A dermoscopic close-up of a skin lesion; the subject is a female aged around 30 — 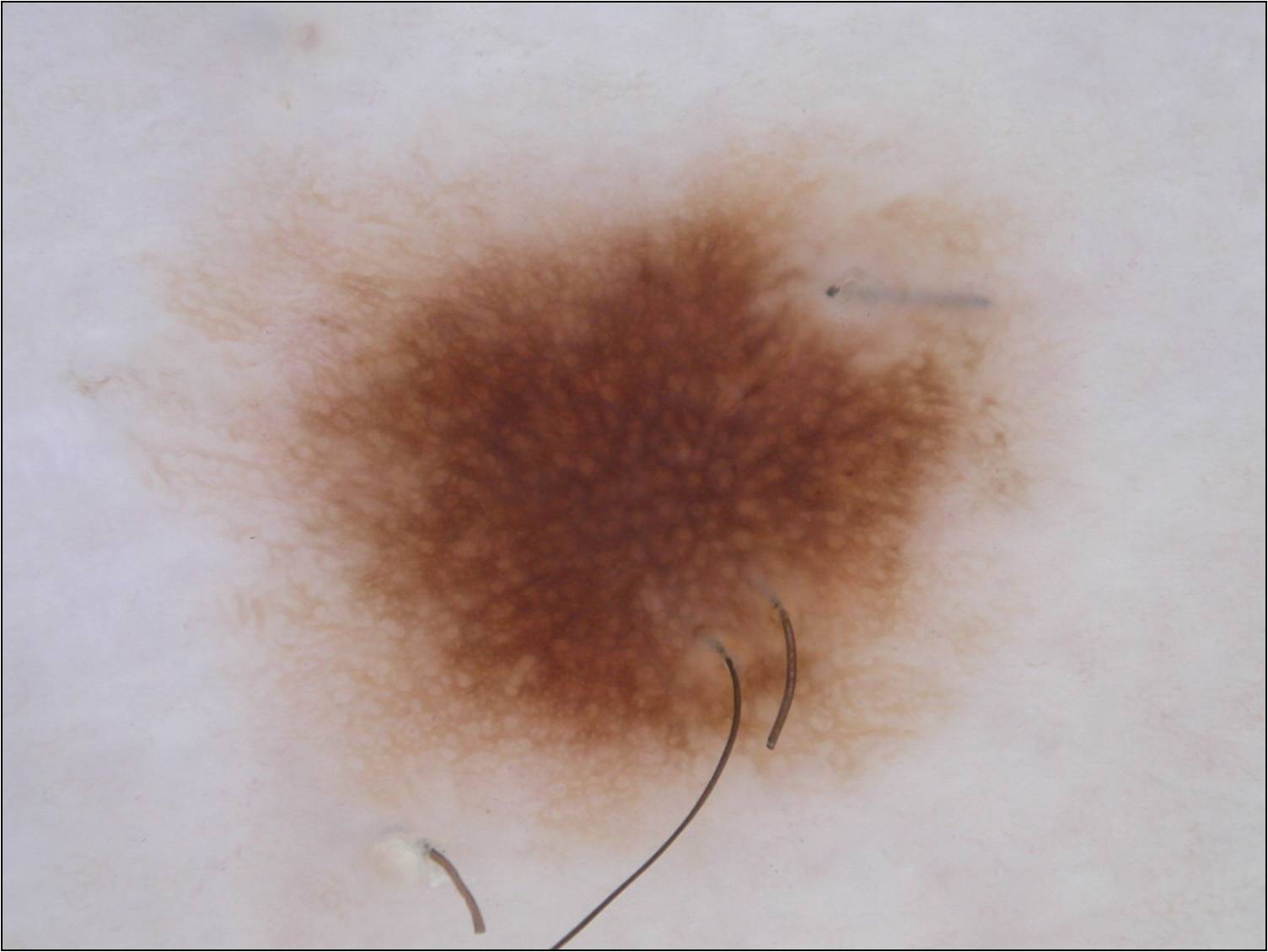Q: Where is the lesion located?
A: <box>117, 128, 1049, 860</box>
Q: Which dermoscopic features were noted?
A: pigment network
Q: Lesion extent?
A: ~43% of the field
Q: What is the diagnosis?
A: a melanocytic nevus, a benign lesion